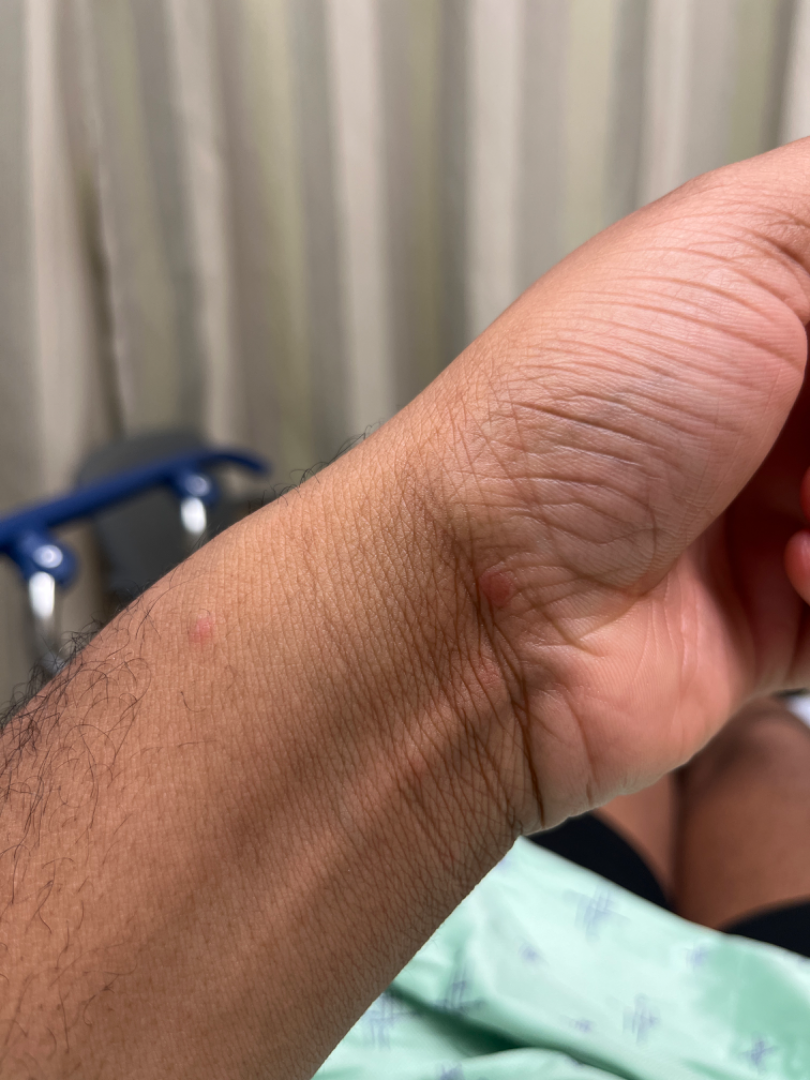{
  "assessment": "ungradable on photographic review",
  "shot_type": "at an angle",
  "body_site": [
    "front of the torso",
    "palm",
    "arm"
  ],
  "patient": "male, age 30–39"
}